Dermoscopy of a skin lesion.
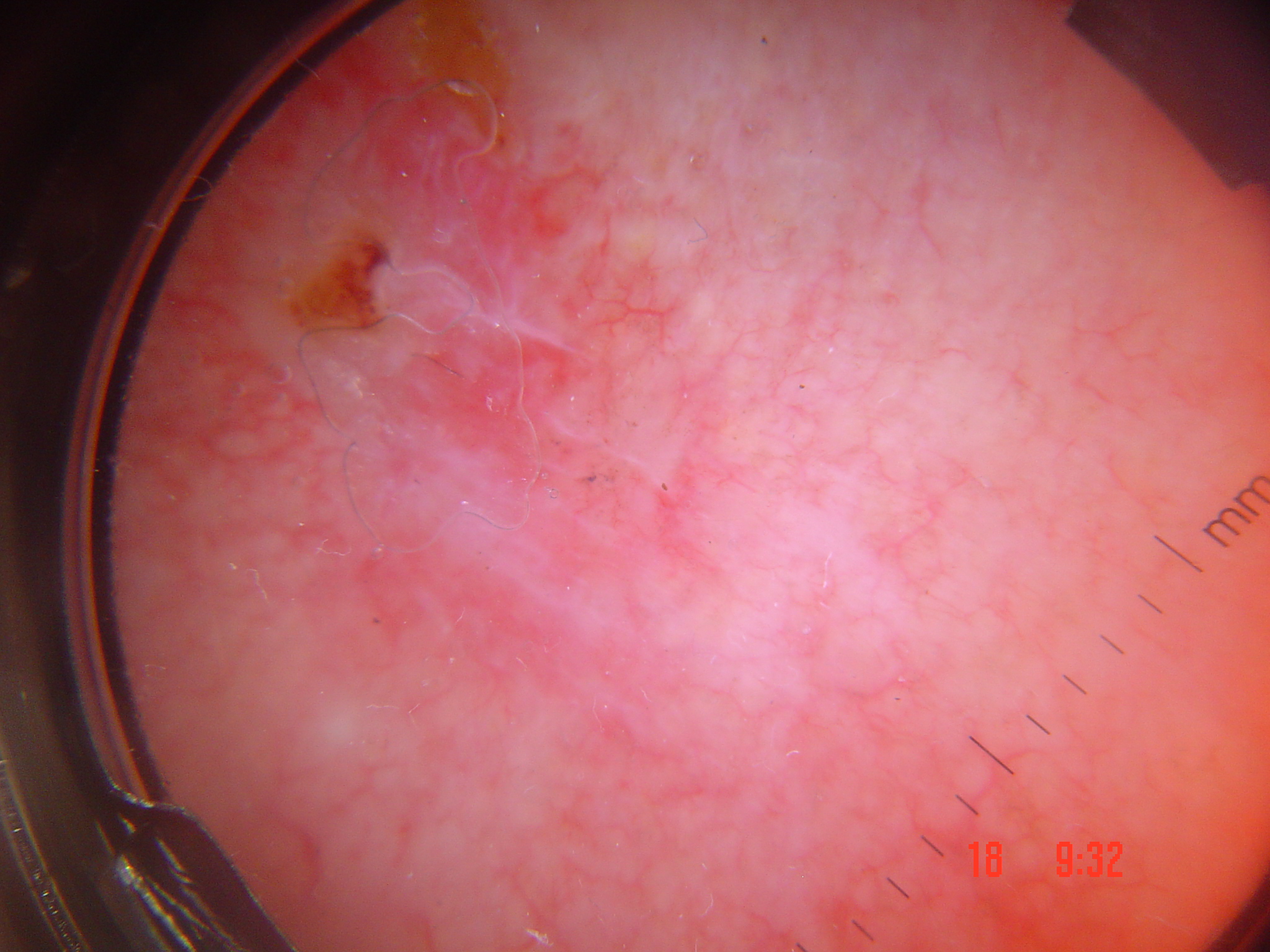Case:
• category: keratinocytic
• pathology: basal cell carcinoma (biopsy-proven)